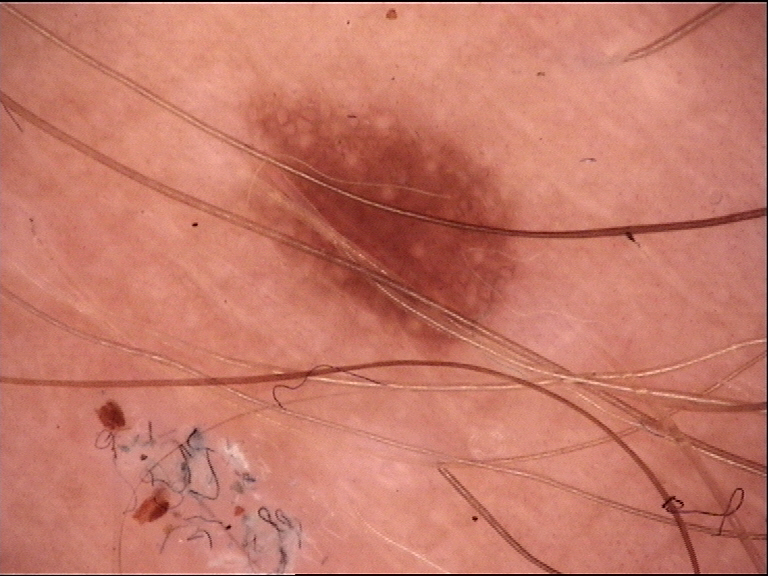Conclusion:
The diagnostic label was a dysplastic junctional nevus.